Imaged for a research study, with no referral diagnosis recorded. The patient says their skin reddens with sun exposure. A dermoscopic image of a skin lesion. Few moles overall by the patient's own estimate — 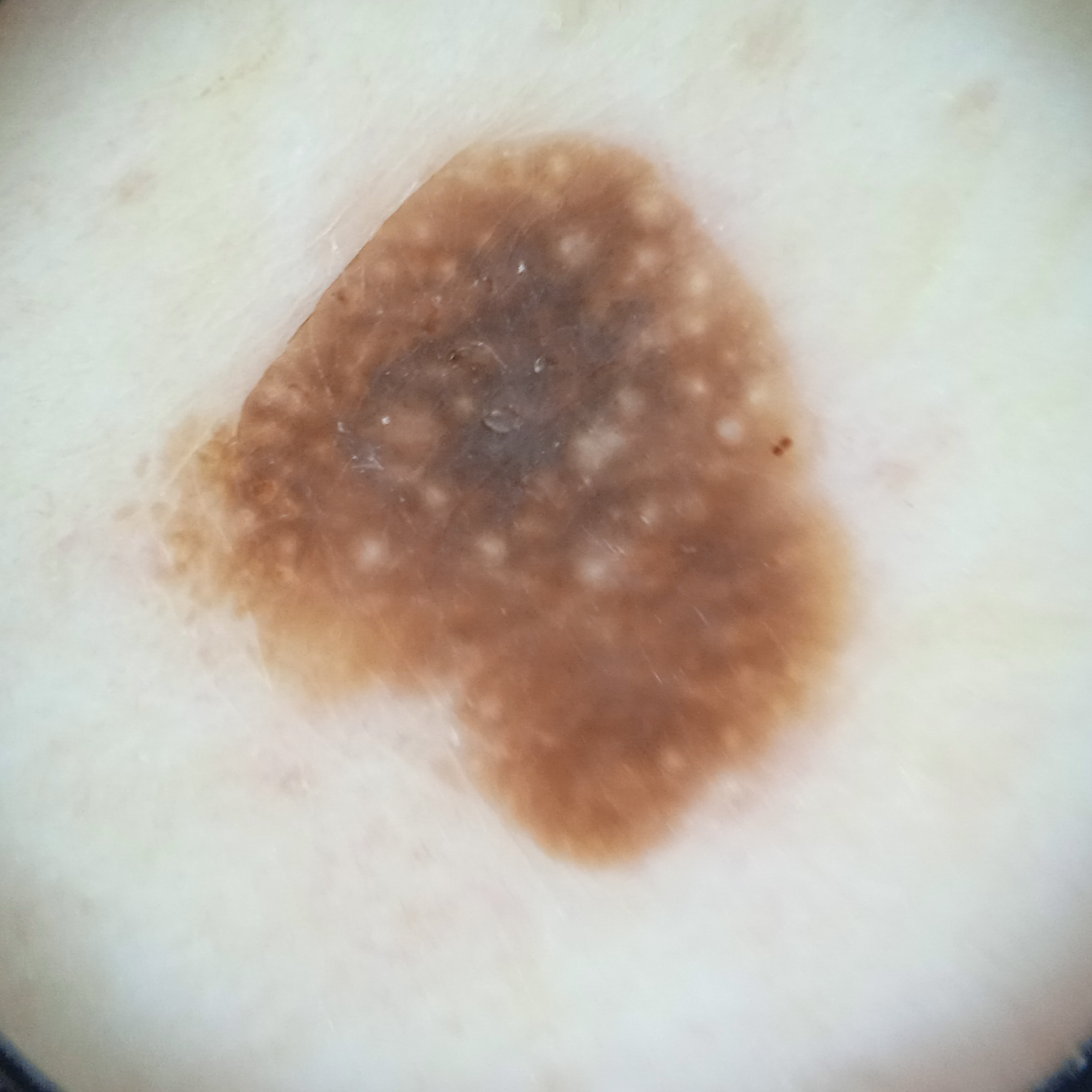On independent review by four dermatologists, the agreed diagnosis was a seborrheic keratosis; the reviewers were highly confident.